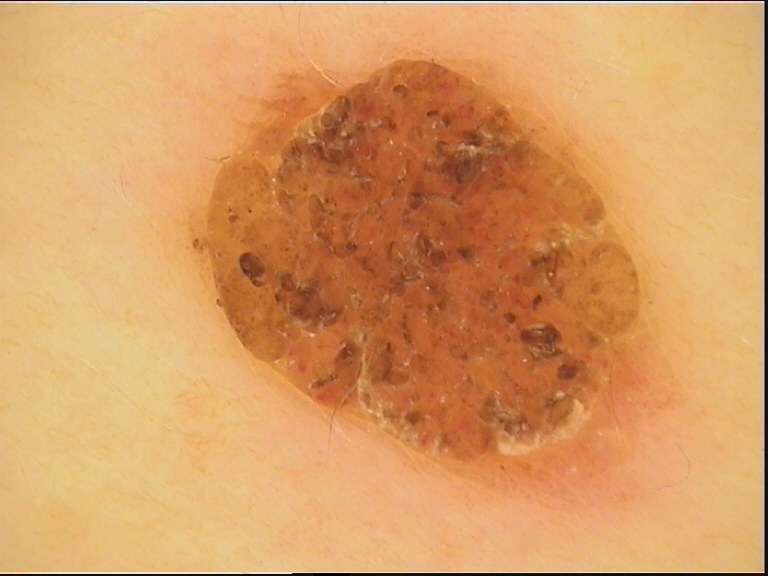label: dermal nevus (expert consensus).